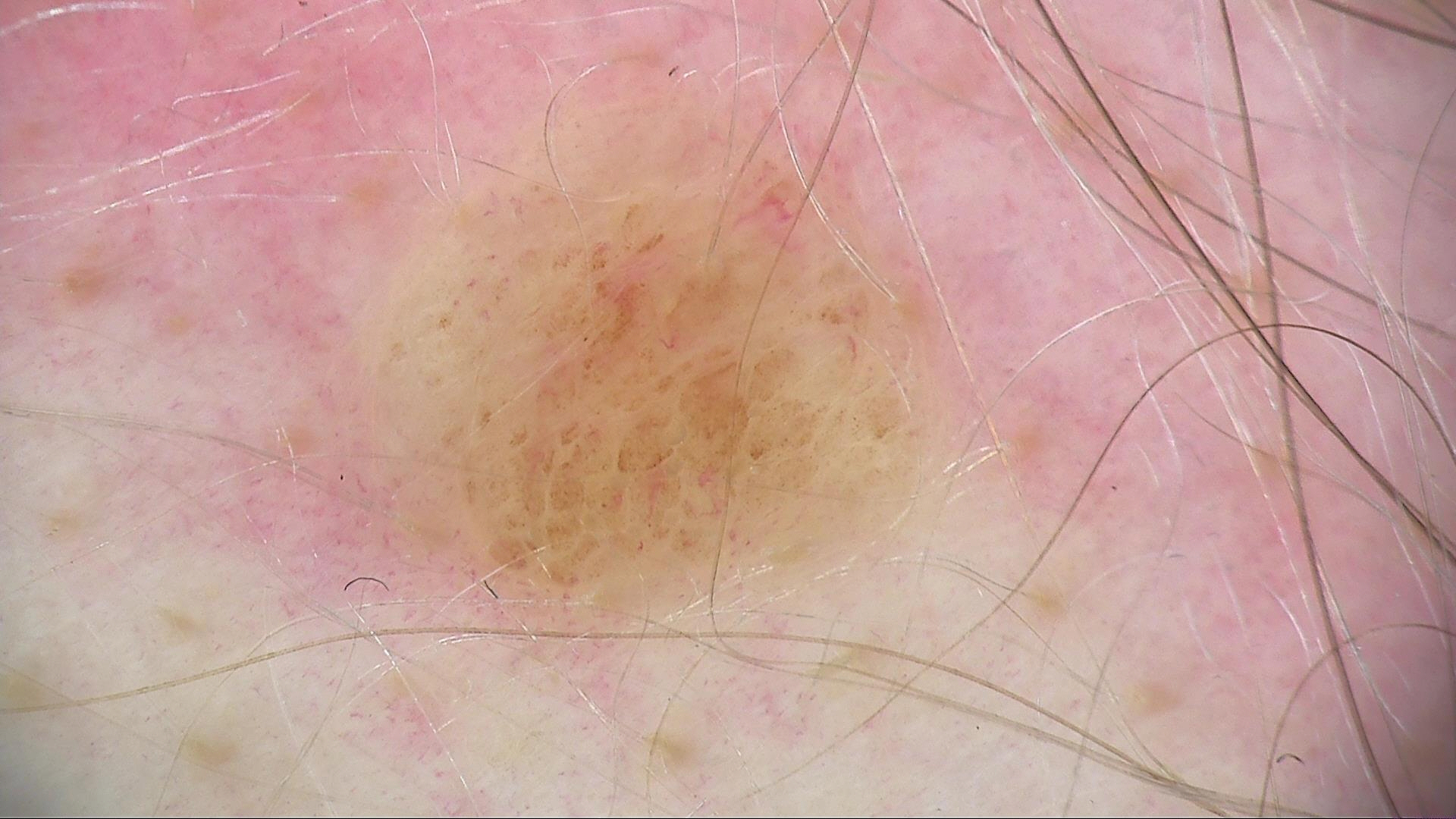Findings:
- diagnosis · compound nevus (expert consensus)